A dermoscopic close-up of a skin lesion.
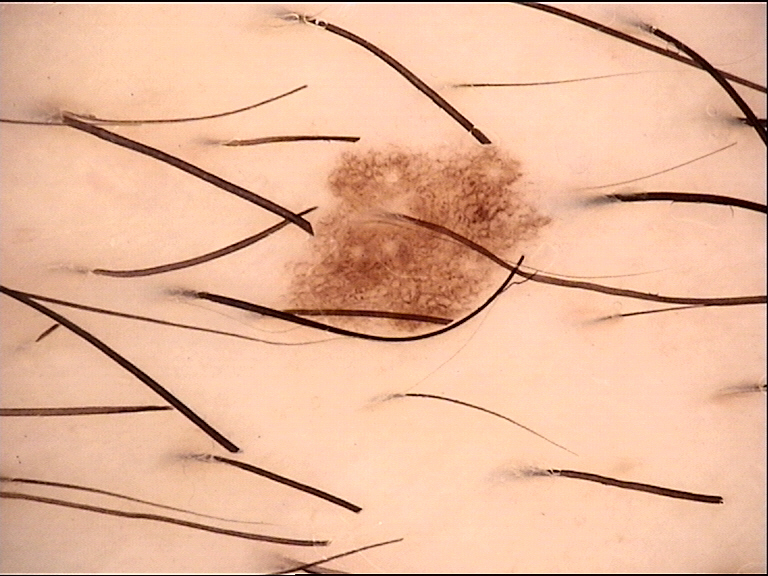* class: dysplastic junctional nevus (expert consensus)